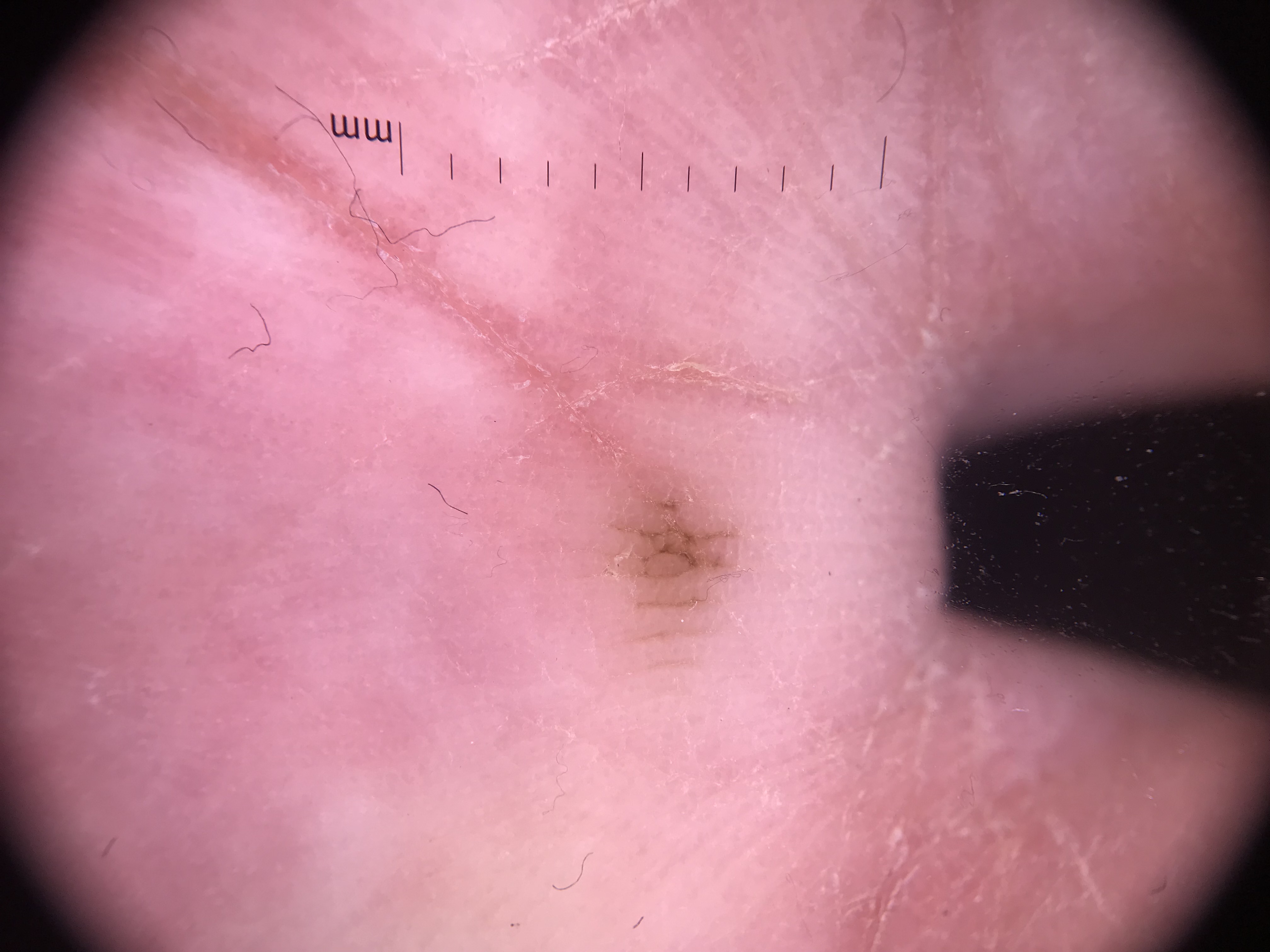{"diagnosis": {"name": "acral junctional nevus", "code": "ajb", "malignancy": "benign", "super_class": "melanocytic", "confirmation": "expert consensus"}}